The photograph was taken at an angle, the affected area is the leg, the patient notes bothersome appearance: 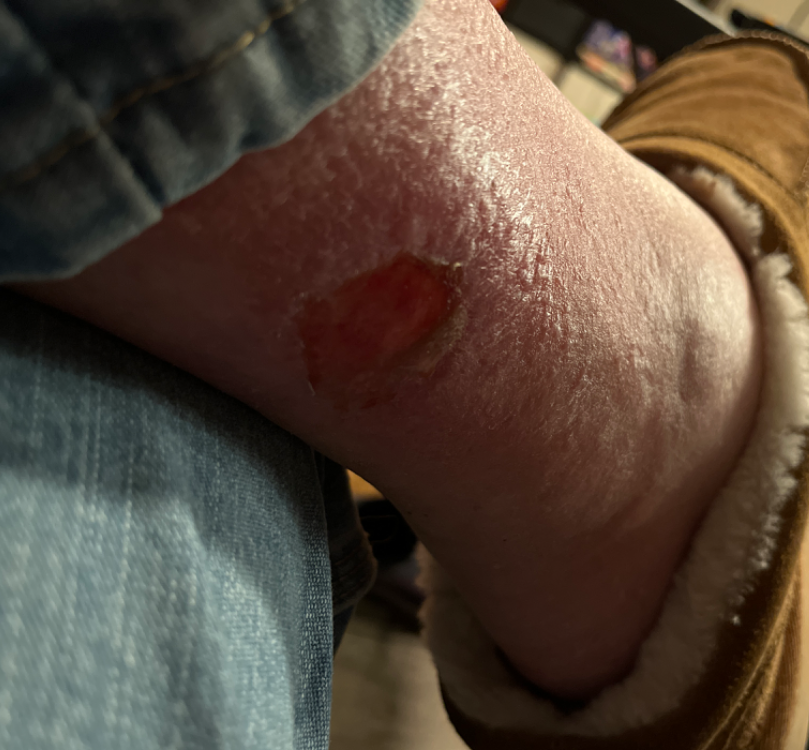Impression: On remote review of the image, the differential is split between Erosion of skin; Abrasion, scrape, or scab; and Traumatic blister.